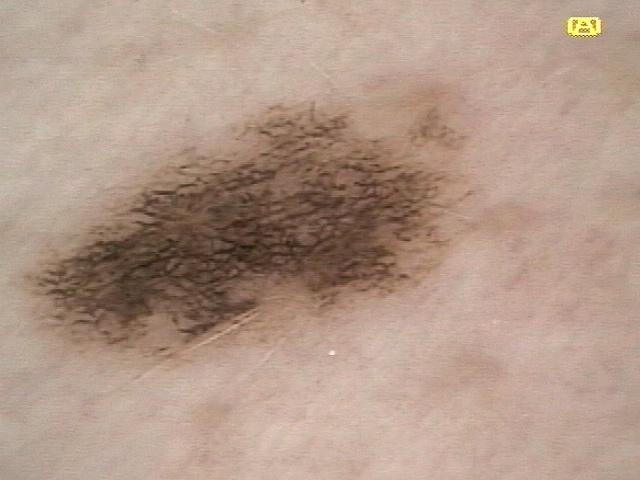| feature | finding |
|---|---|
| modality | contact-polarized dermoscopy |
| patient | female, aged approximately 50 |
| body site | an upper extremity |
| assessment | Nevus |